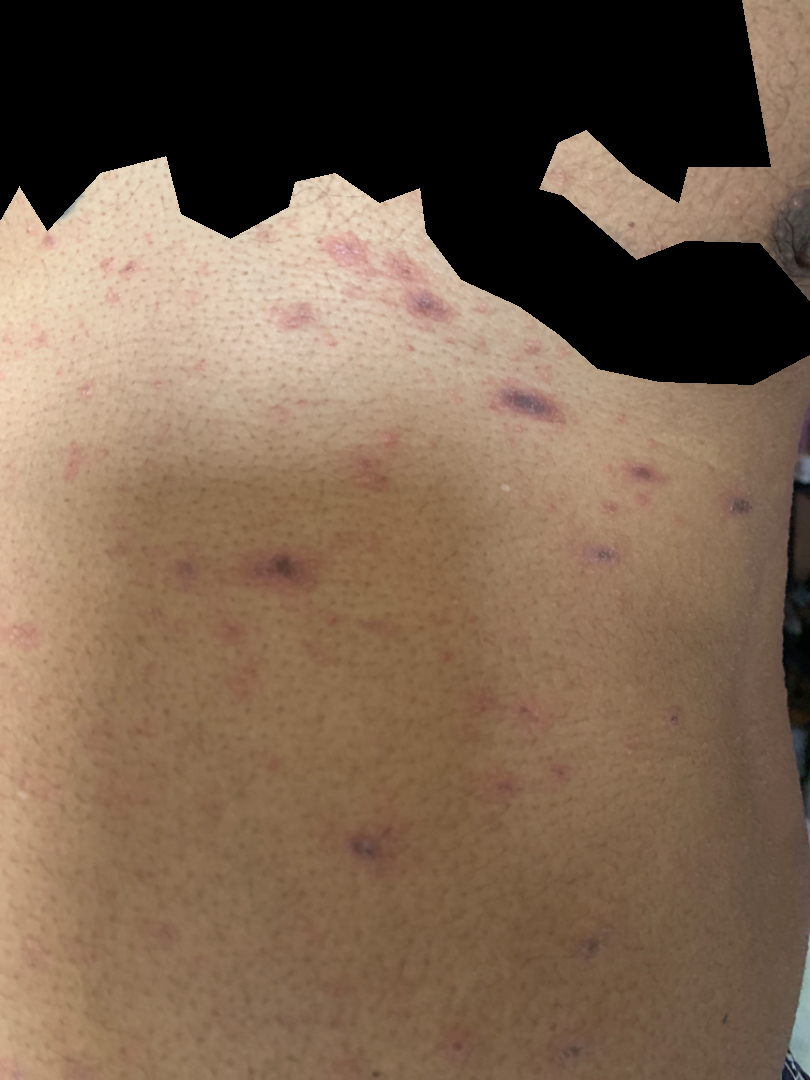{"differential": {"leading": ["Erythema multiforme"], "considered": ["Pityriasis lichenoides"], "unlikely": ["Drug Rash"]}}